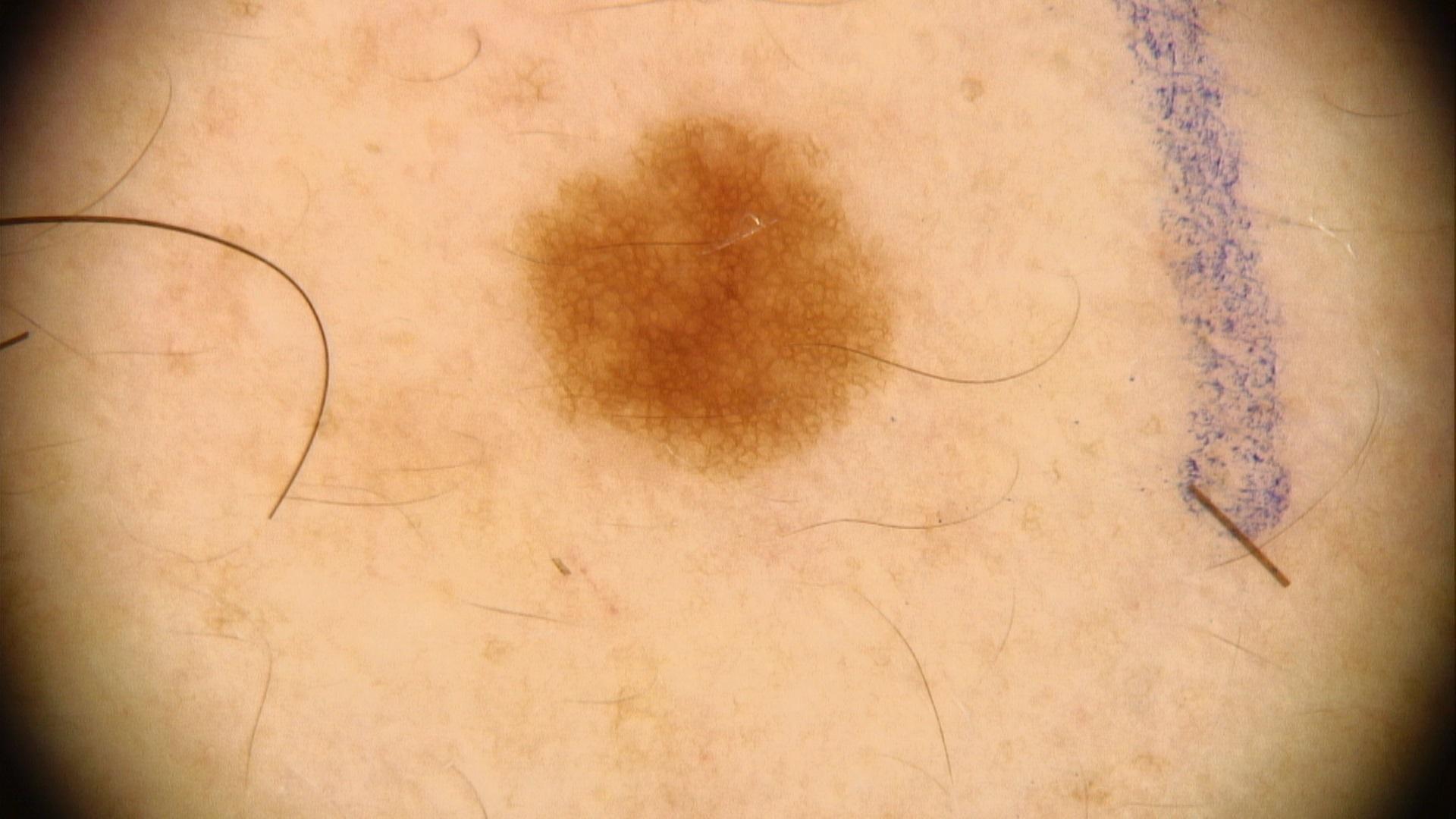patient=male, roughly 40 years of age; image=dermoscopic image; location=an upper extremity; diagnostic label=Nevus (clinical impression).